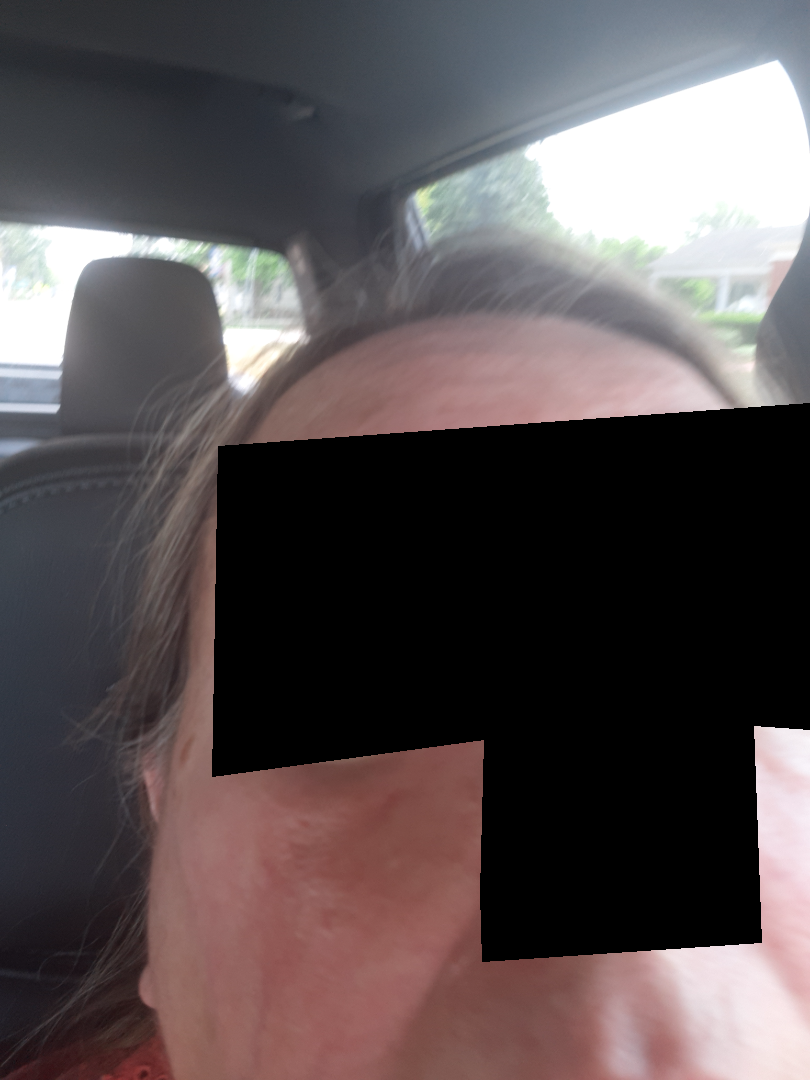Q: Could the case be diagnosed?
A: could not be assessed
Q: How was the photo taken?
A: close-up